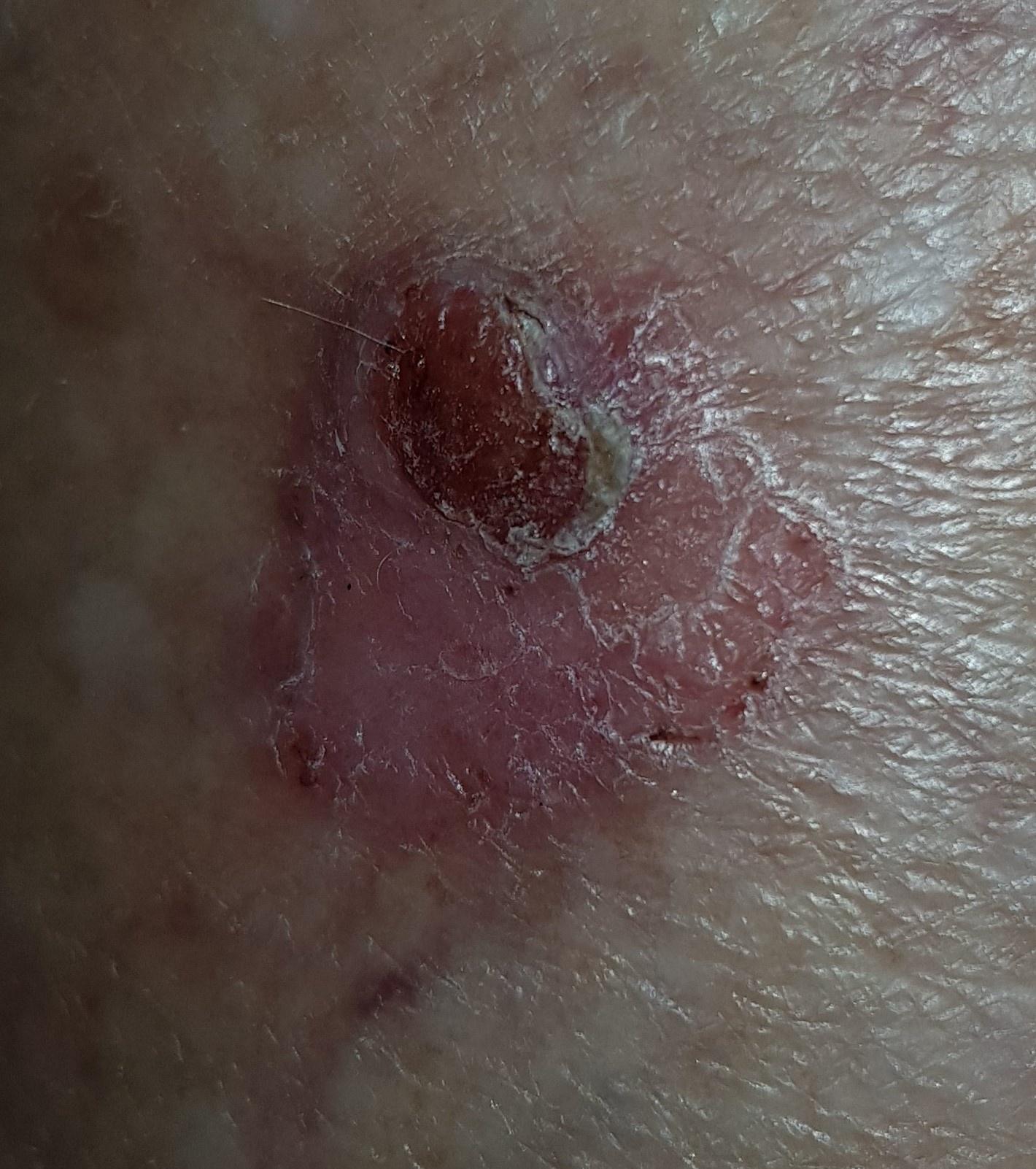pathology: Basal cell carcinoma (biopsy-proven).